A dermoscopic photograph of a skin lesion:
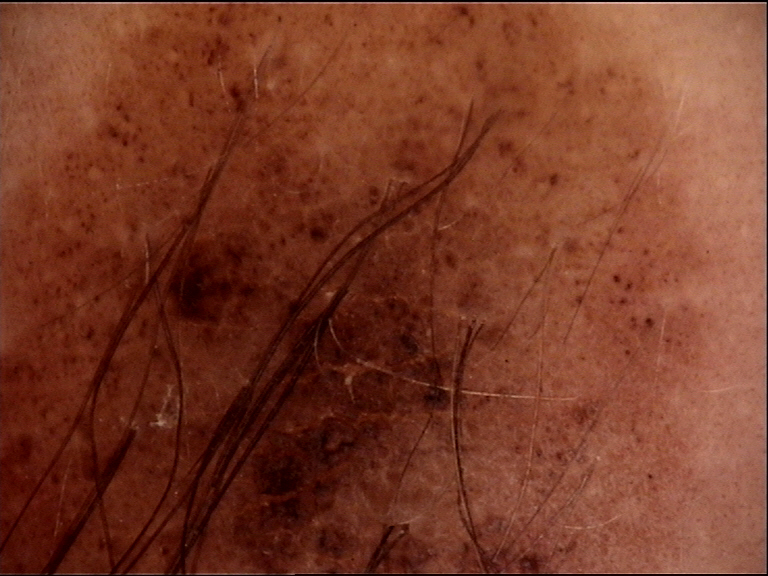| field | value |
|---|---|
| classification | banal |
| label | congenital compound nevus (expert consensus) |